No relevant systemic symptoms. The subject is 50–59, male. The photograph is a close-up of the affected area. The lesion is associated with bothersome appearance. The contributor notes the lesion is raised or bumpy. The contributor notes the condition has been present for less than one week. The arm is involved. The patient considered this a rash.
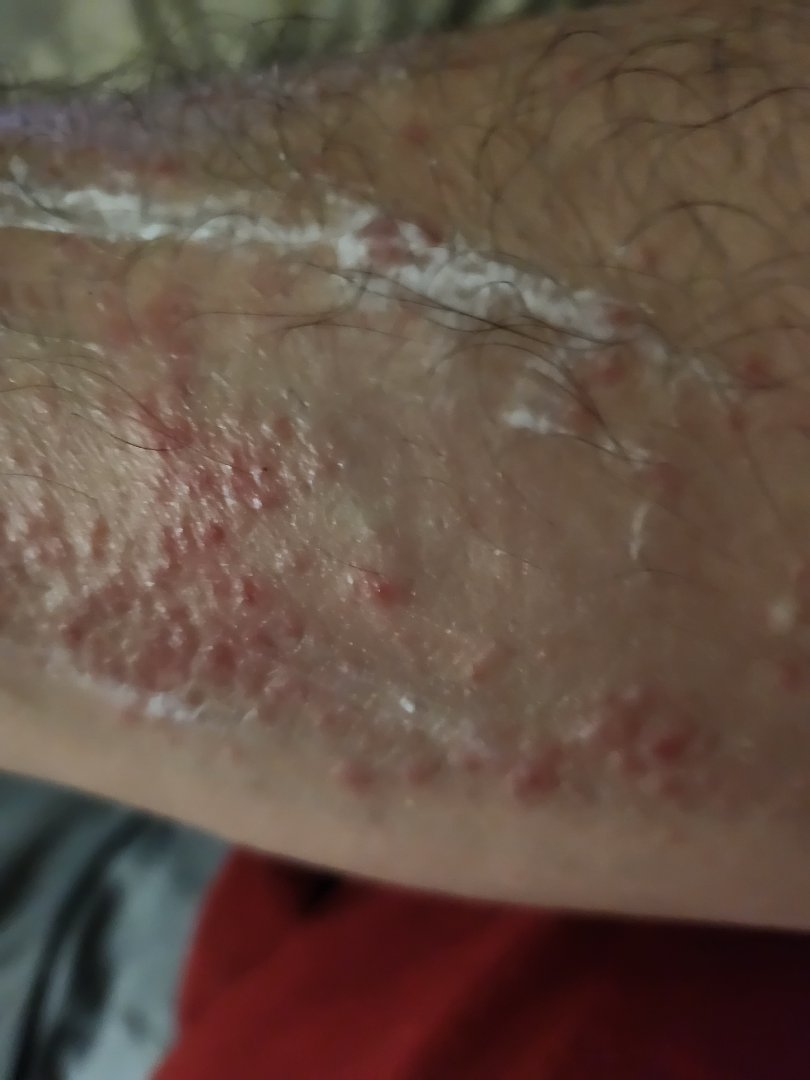Review:
On remote review of the image: most likely Allergic Contact Dermatitis; with consideration of Scabies; also raised was Insect Bite.